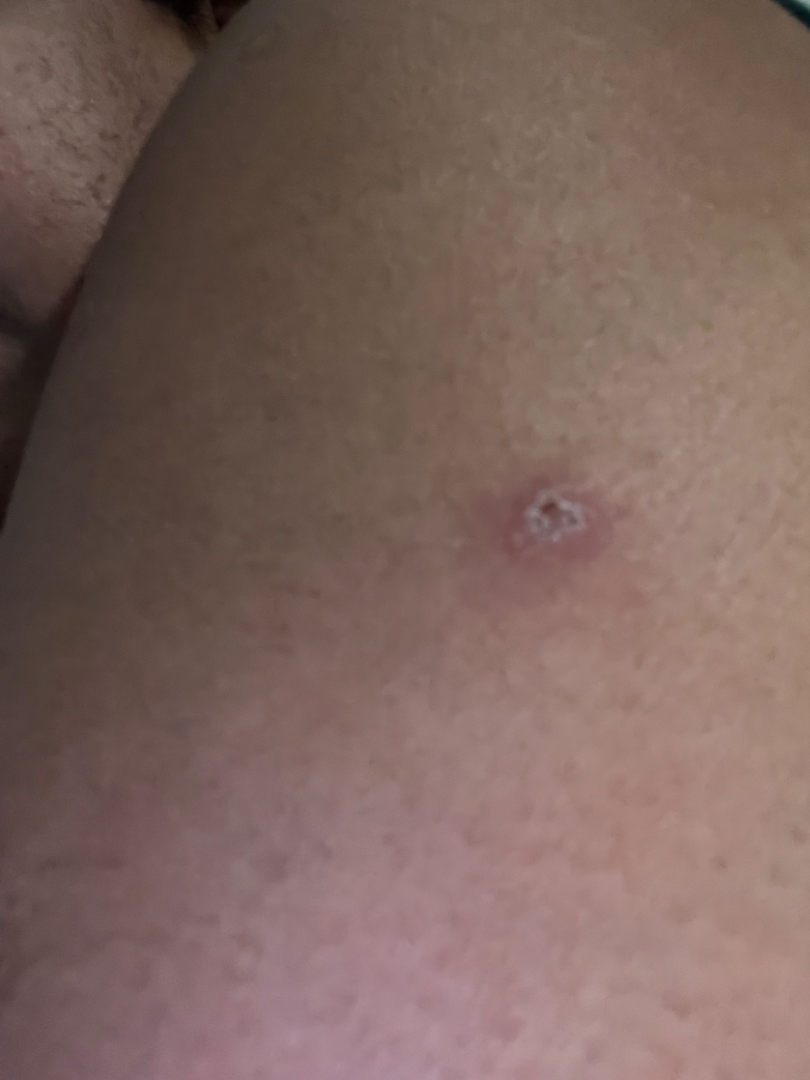Q: Could the case be diagnosed?
A: could not be assessed
Q: When did this start?
A: less than one week
Q: What is the affected area?
A: arm and head or neck
Q: How does the lesion feel?
A: raised or bumpy
Q: What is the framing?
A: close-up